A smartphone photograph of a skin lesion. A female subject in their early 60s. History notes alcohol use and prior skin cancer (patient or family) — 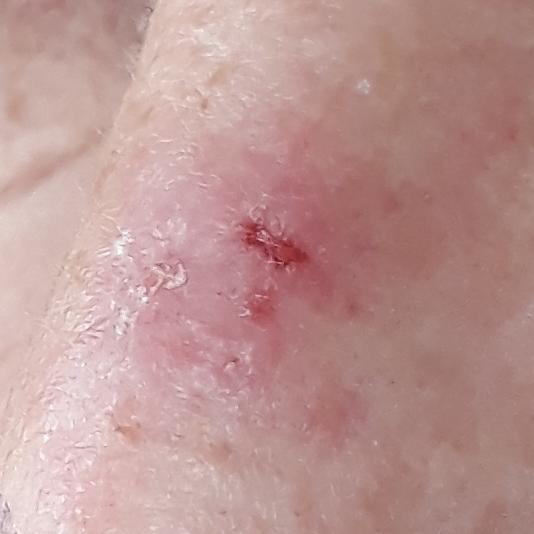body site: the nose
lesion diameter: 5x4 mm
patient-reported symptoms: itching, bleeding
pathology: basal cell carcinoma (biopsy-proven)